The patient described the issue as a rash, an image taken at an angle, texture is reported as flat, reported lesion symptoms include enlargement, reported duration is one to four weeks — 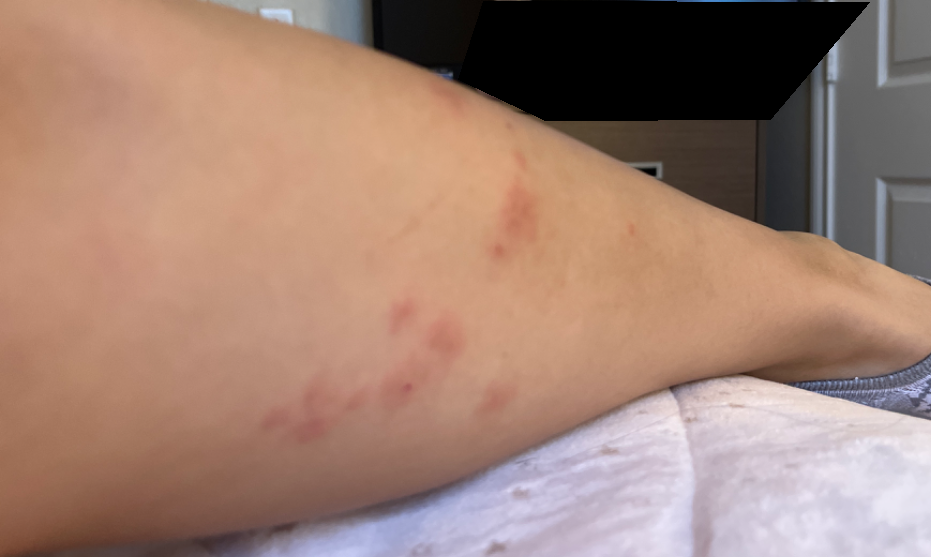Q: What was the assessment?
A: ungradable on photographic review